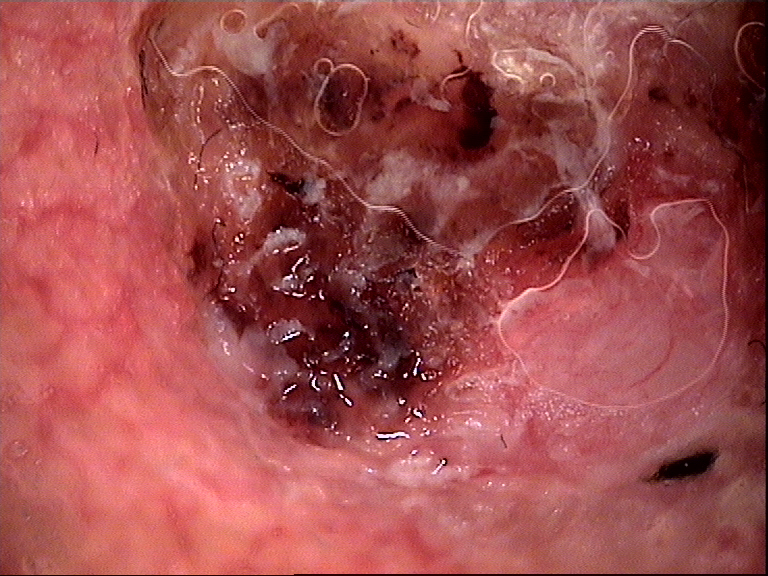Findings:
• subtype — keratinocytic
• class — squamous cell carcinoma (biopsy-proven)